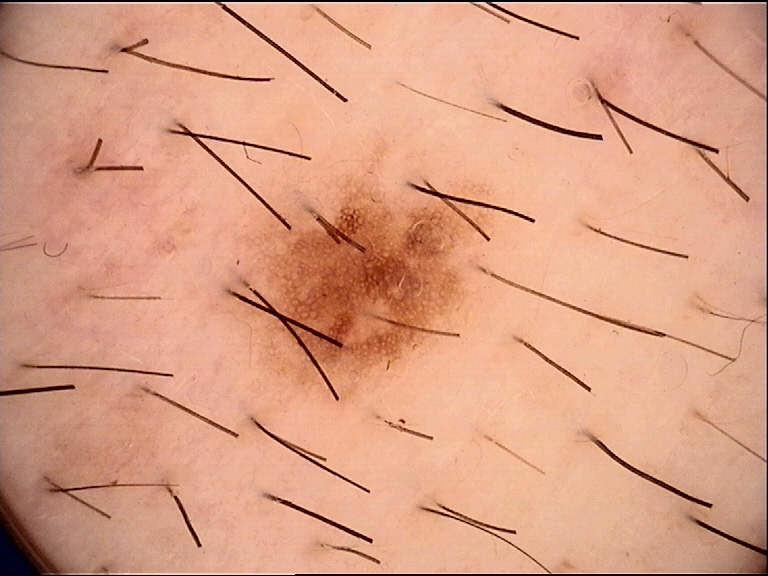image type: dermoscopy, diagnostic label: dysplastic junctional nevus (expert consensus).